Dermoscopy of a skin lesion: 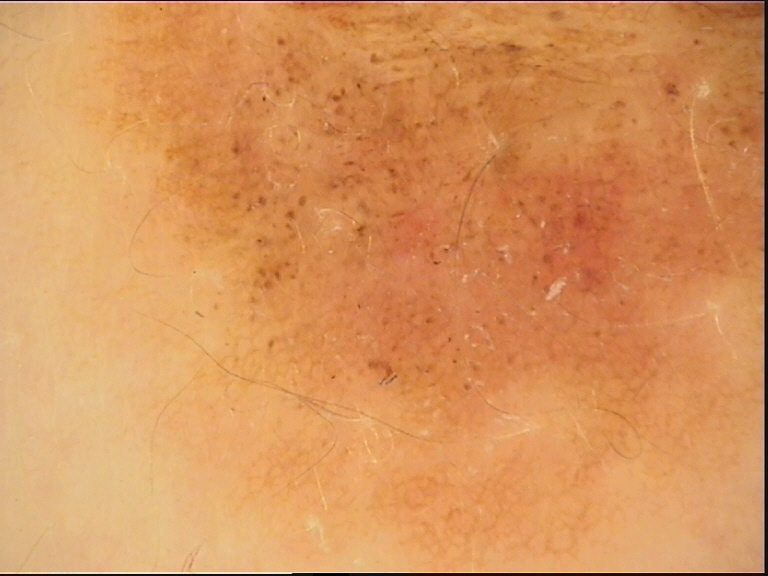Labeled as a banal lesion — a congenital compound nevus.